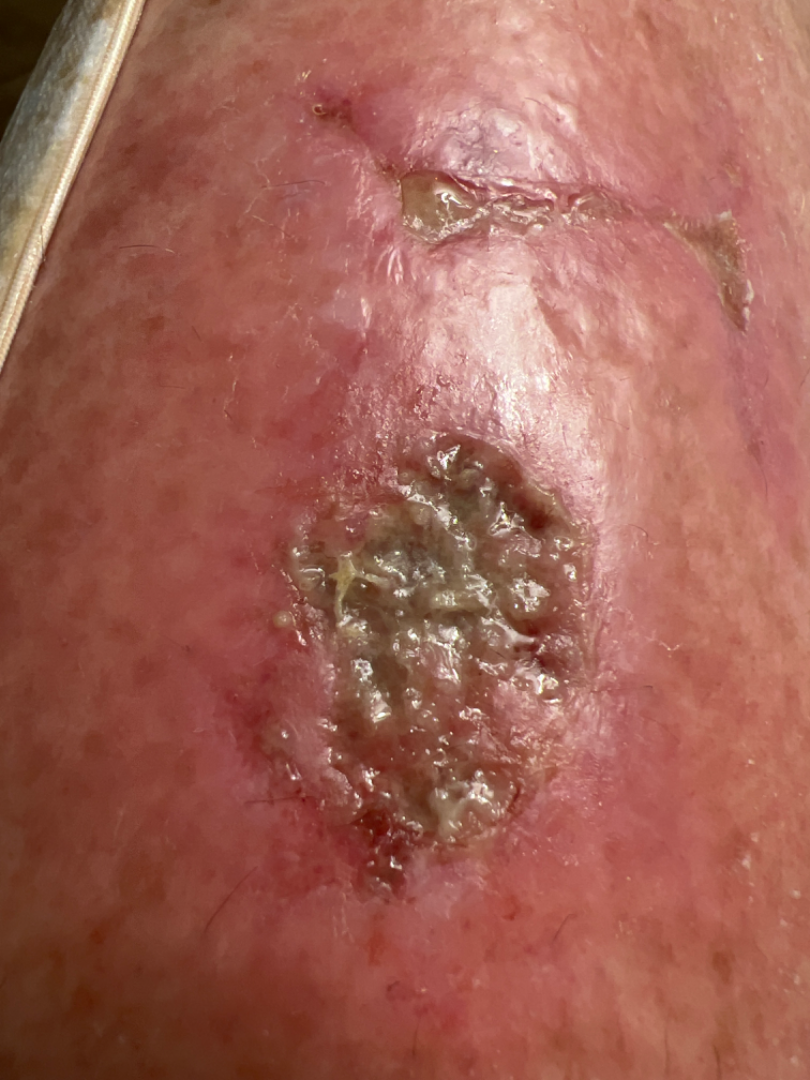The reviewing dermatologist was unable to assign a differential diagnosis from the image. The subject is 60–69, female. The lesion involves the leg. The photograph was taken at an angle.